A macroscopic clinical photograph of a skin lesion; a male patient age 83.
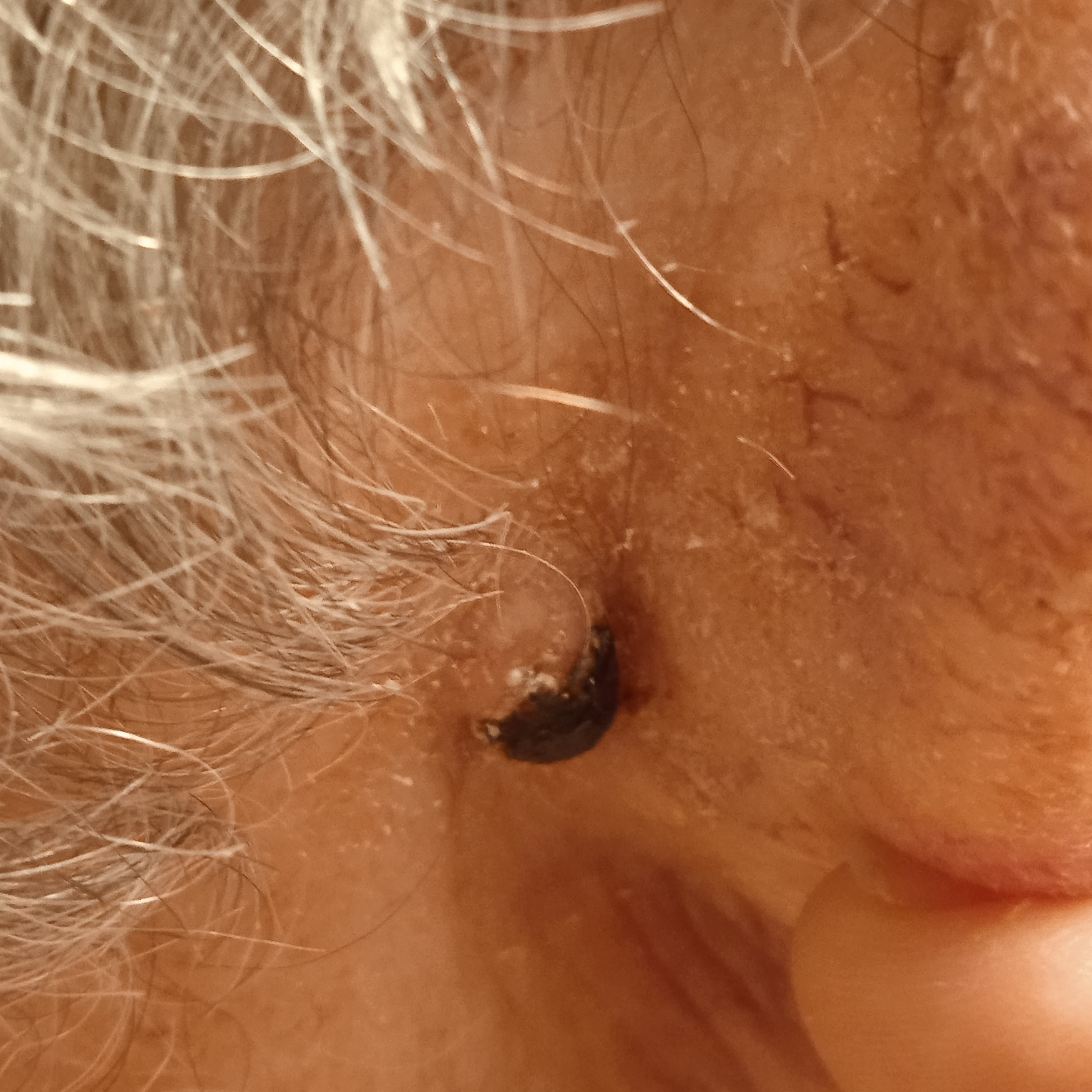<case>
  <lesion_location>the head</lesion_location>
  <lesion_size>
    <diameter_mm>8.0</diameter_mm>
  </lesion_size>
  <diagnosis>
    <name>basal cell carcinoma</name>
    <malignancy>malignant</malignancy>
    <procedure>excision</procedure>
    <tumor_thickness_mm>2.7</tumor_thickness_mm>
  </diagnosis>
</case>